A dermatoscopic image of a skin lesion.
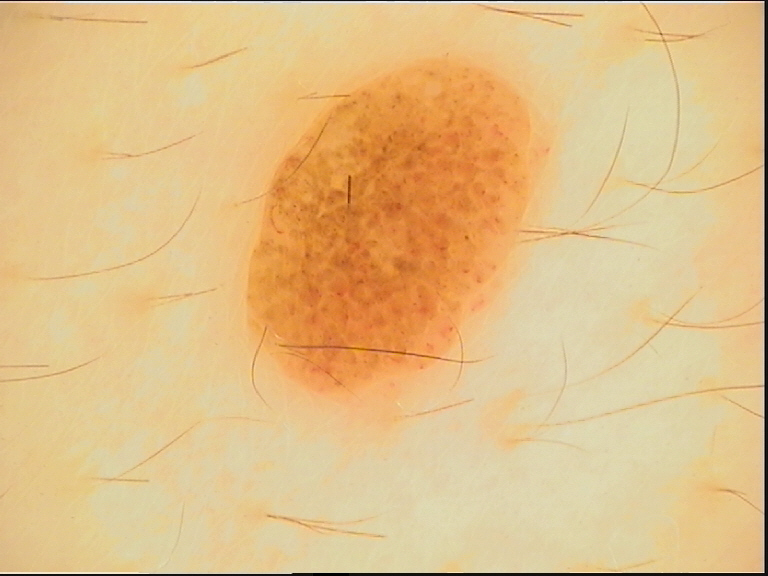Findings: The architecture is that of a banal lesion. Impression: Consistent with a compound nevus.